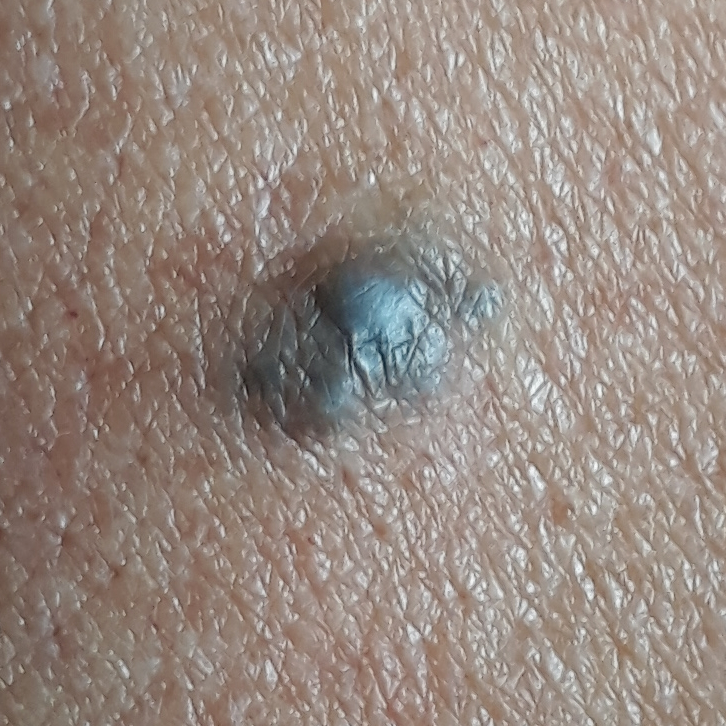Patient and lesion:
Recorded as Fitzpatrick IV. A male patient in their 50s. A clinical close-up photograph of a skin lesion. The lesion involves an arm. The lesion is roughly 6 by 4 mm. Per patient report, the lesion is elevated.
Diagnosis:
Histopathological examination showed a benign lesion — a nevus.